A dermoscopy image of a single skin lesion.
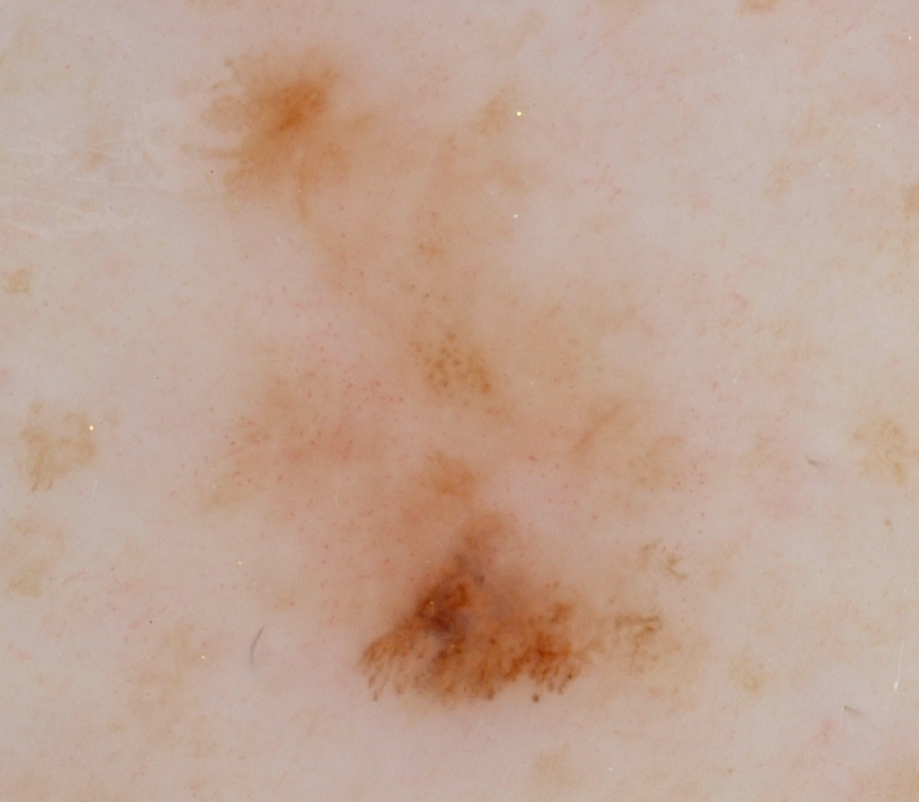Q: How much of the field does the lesion occupy?
A: ~26% of the field
Q: Which dermoscopic features were noted?
A: streaks and globules; absent: milia-like cysts, pigment network, and negative network
Q: Where is the lesion located?
A: x1=202 y1=41 x2=693 y2=718
Q: What is this lesion?
A: a melanoma, a malignant lesion